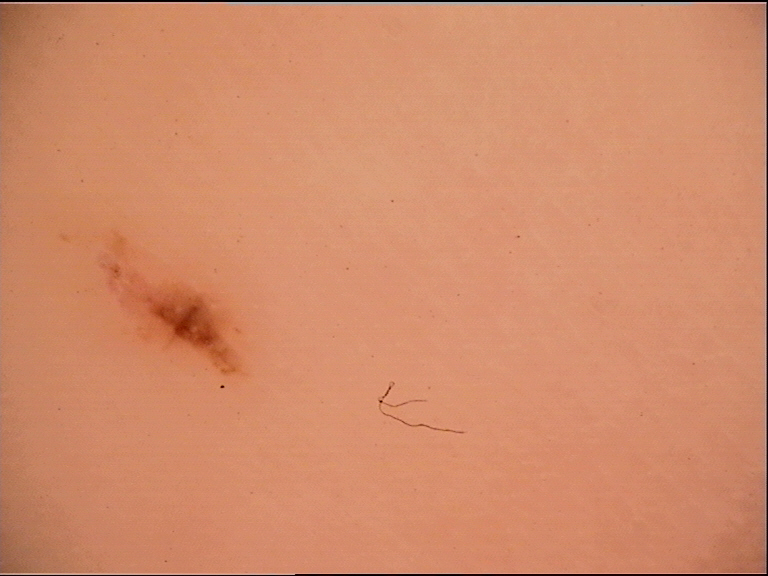Conclusion:
Classified as an acral junctional nevus.